The photograph is a close-up of the affected area:
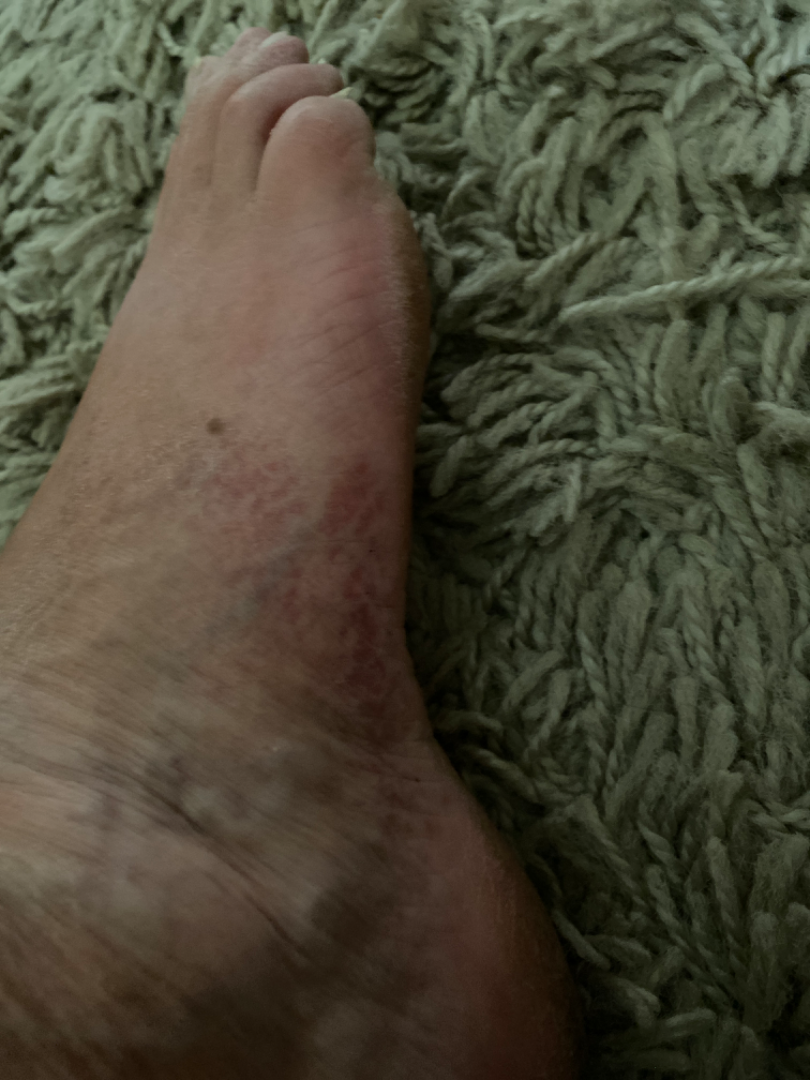assessment: indeterminate from the photograph